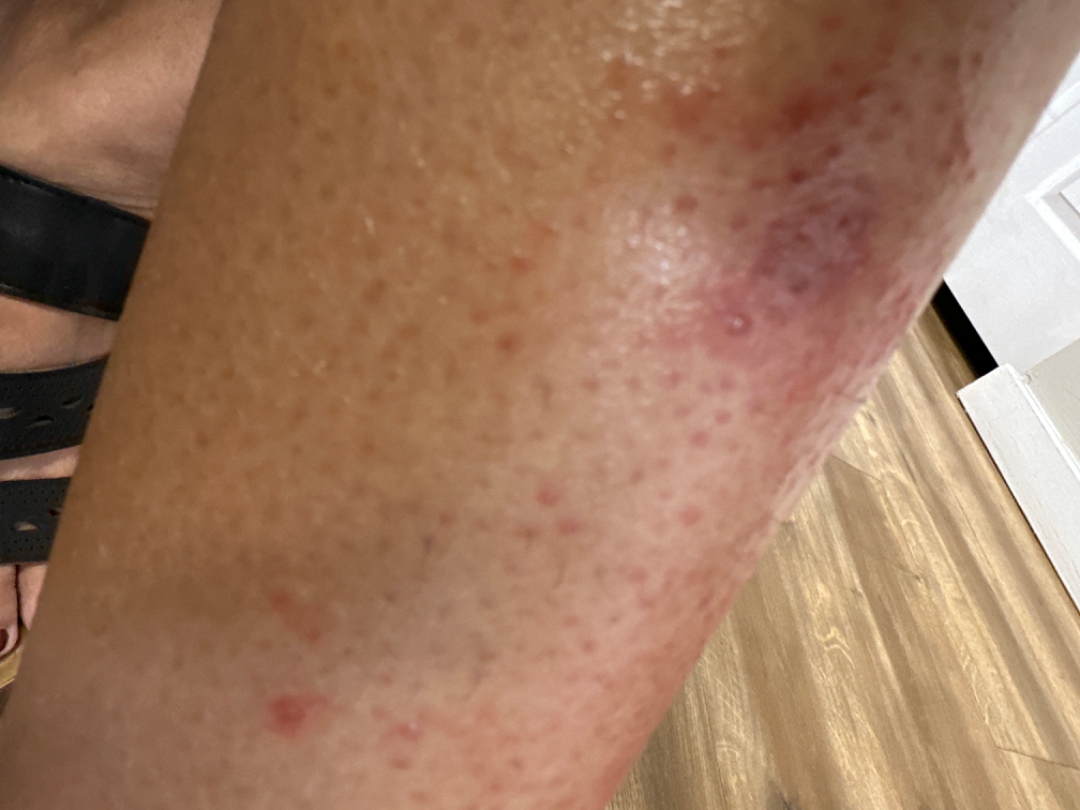The image was not sufficient for the reviewer to characterize the skin condition.